The photo was captured at a distance — 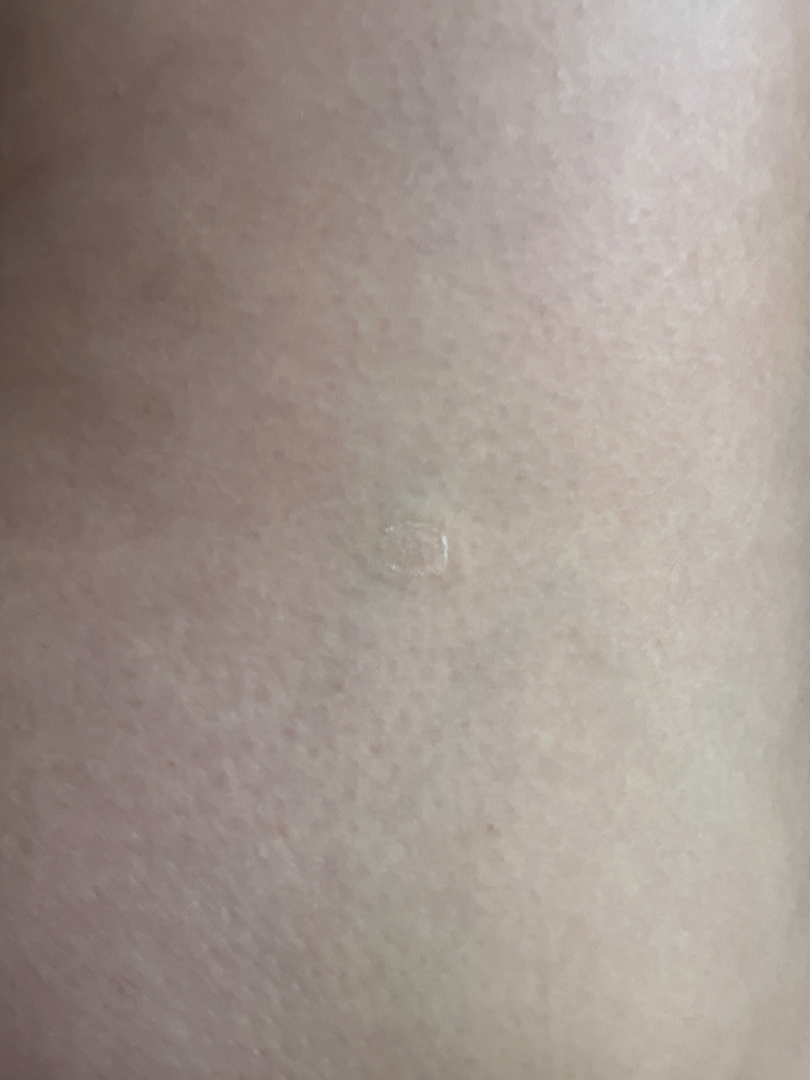Q: What is the dermatologist's impression?
A: the impression was split between Porokeratosis, Xerosis and Keratosis